A skin lesion imaged with a dermatoscope.
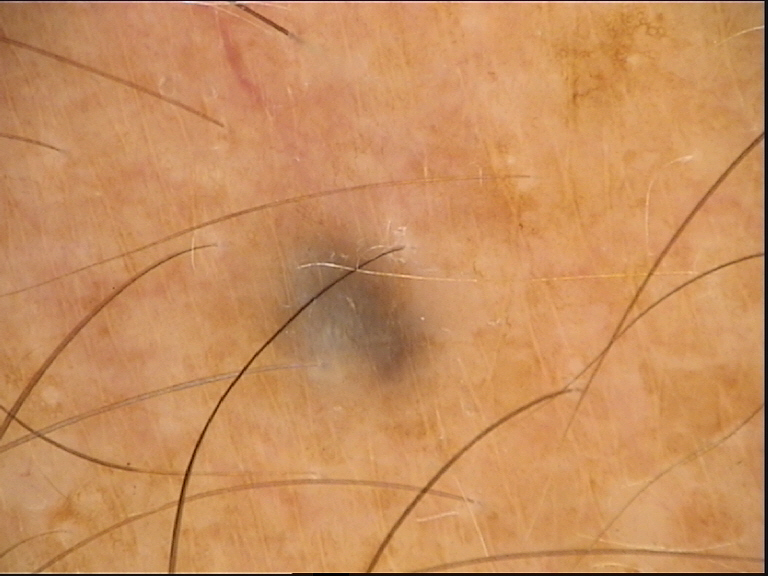  diagnosis:
    name: blue nevus
    code: bdb
    malignancy: benign
    super_class: melanocytic
    confirmation: expert consensus